The photograph was taken at an angle; the back of the hand, arm, top or side of the foot, front of the torso, back of the torso and leg are involved; male patient, age 18–29.
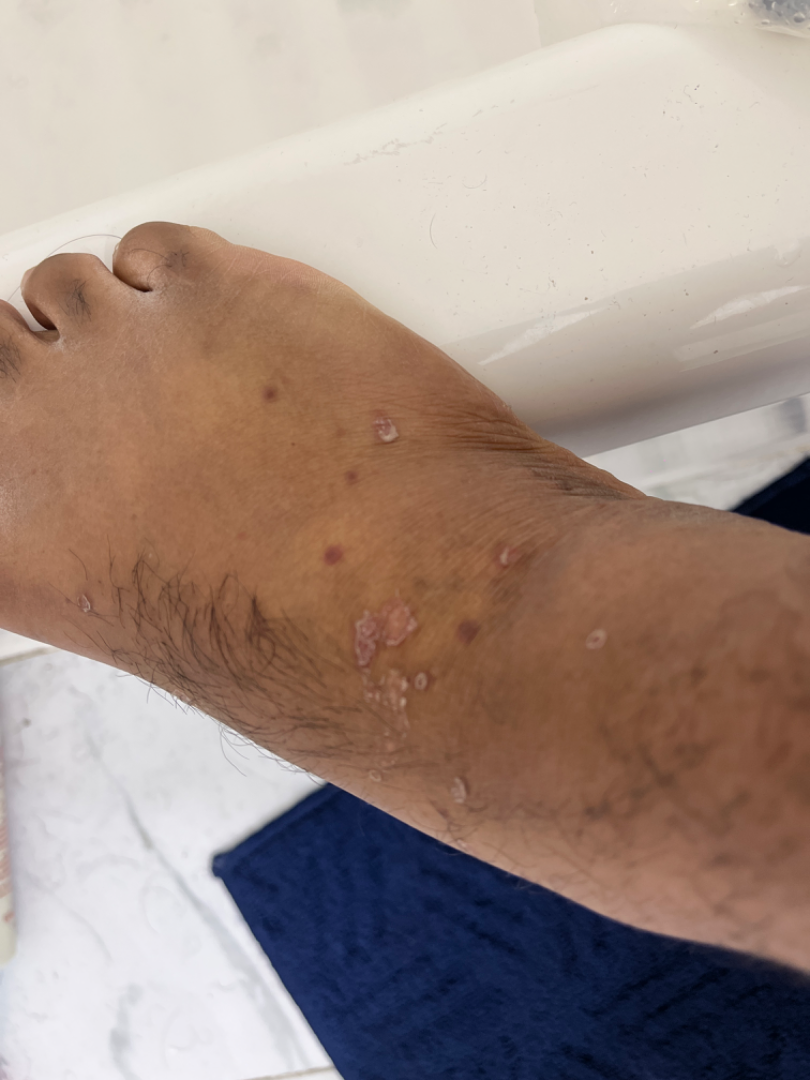self-categorized as — a rash | patient-reported symptoms — bothersome appearance, darkening, enlargement and itching | symptom duration — one to four weeks | lesion texture — raised or bumpy | other reported symptoms — none reported | assessment — Folliculitis (favored); Psoriasis (less likely); Perifolliculitis (less likely).